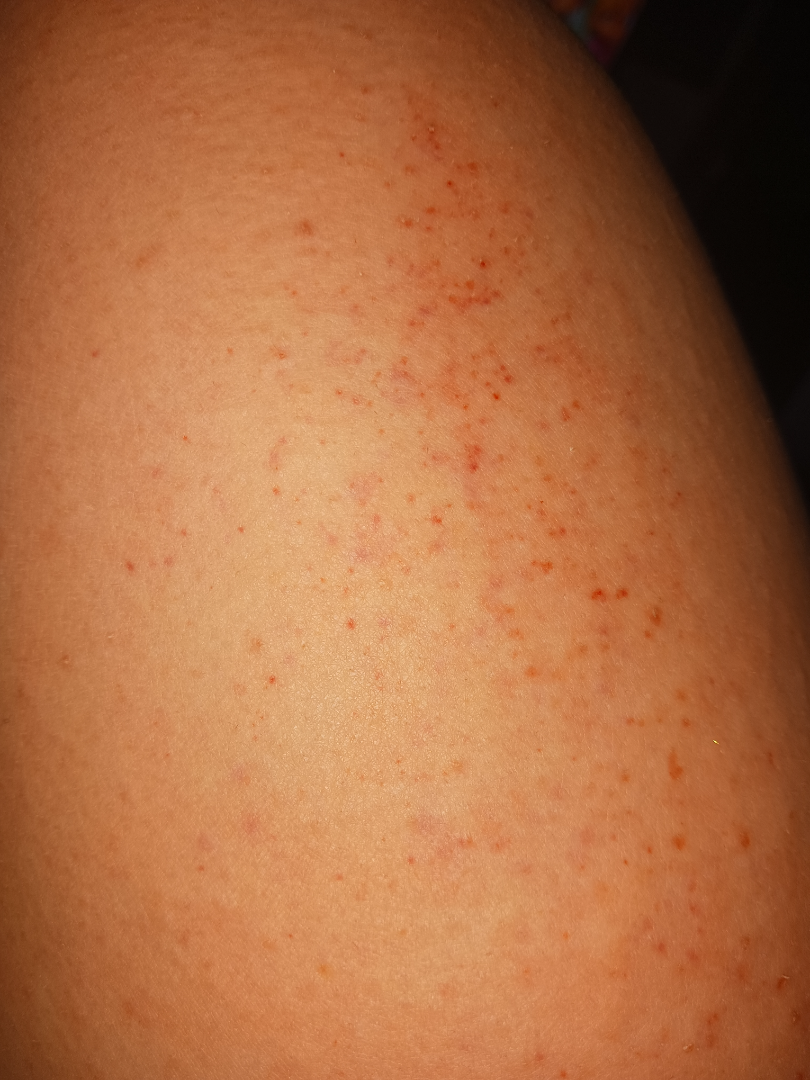Close-up view. The leg is involved. The contributor is female. On photographic review, the leading impression is Purpura; an alternative is Pigmented purpuric eruption.